A dermoscopic close-up of a skin lesion.
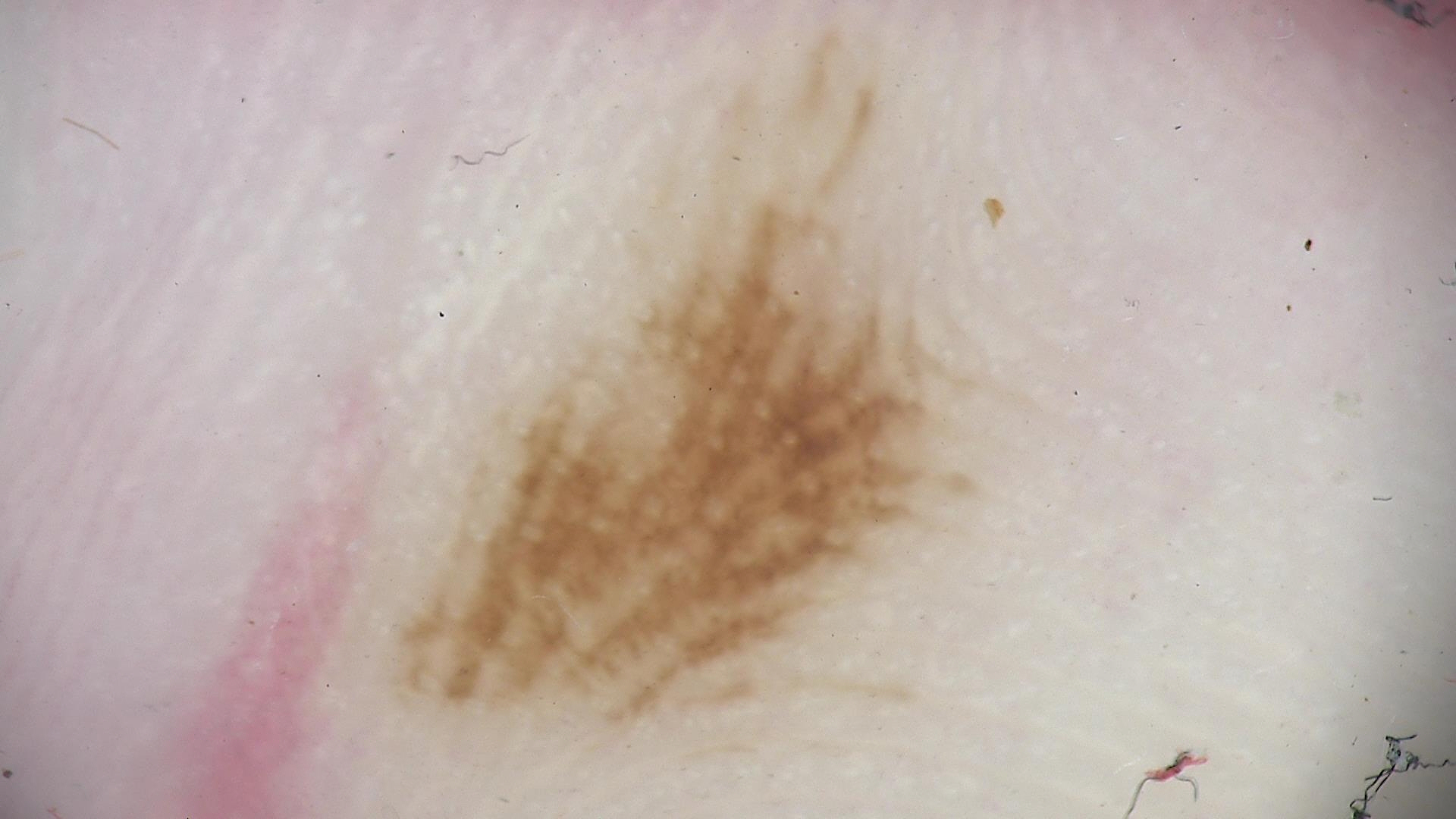{"diagnosis": {"name": "acral dysplastic junctional nevus", "code": "ajd", "malignancy": "benign", "super_class": "melanocytic", "confirmation": "expert consensus"}}